Present for one to four weeks · the affected area is the back of the hand, top or side of the foot, leg, sole of the foot and arm · an image taken at a distance · the lesion is described as flat — 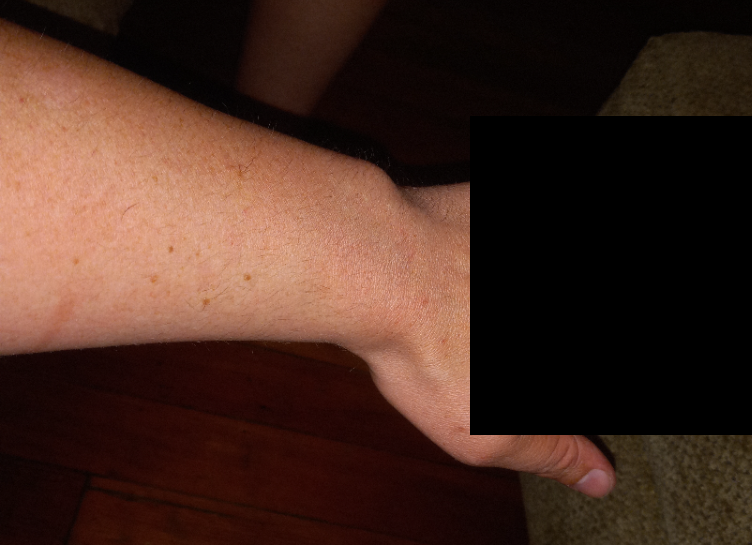Findings:
– assessment: indeterminate from the photograph